A dermoscopic image of a skin lesion.
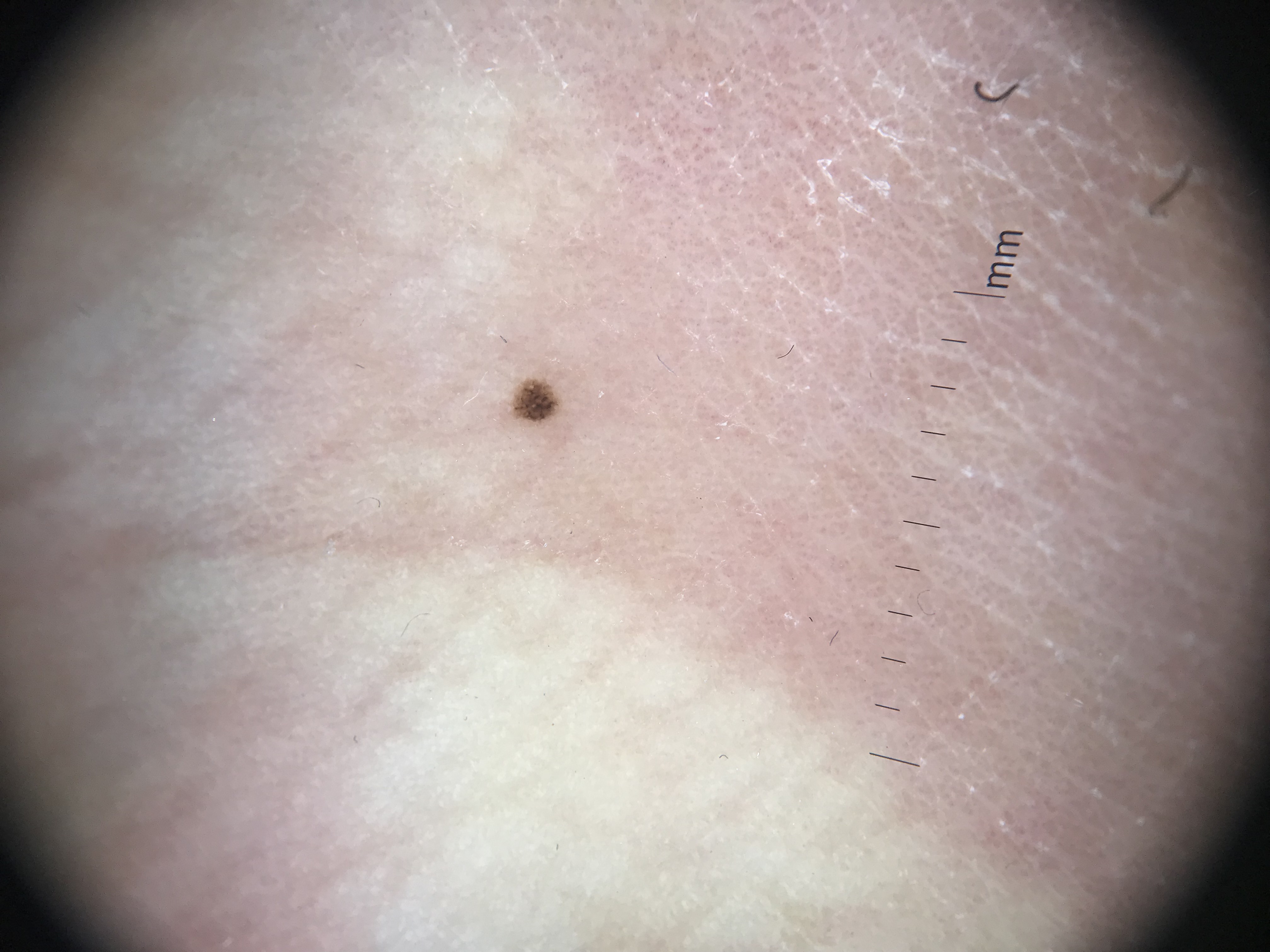The diagnostic label was a benign lesion — an acral dysplastic junctional nevus.